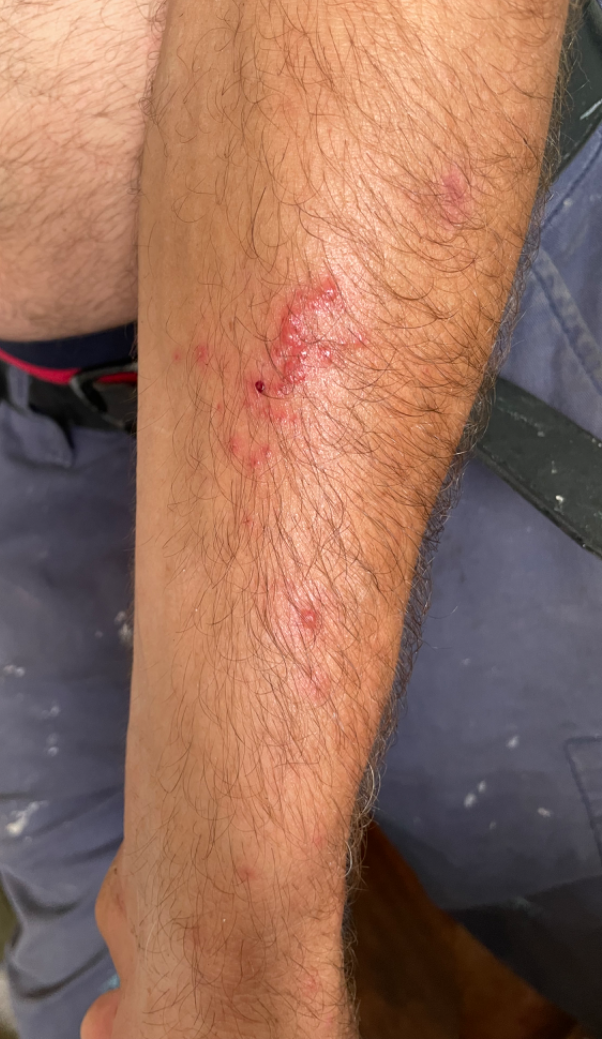  symptoms: itching
  systemic_symptoms: none reported
  shot_type: close-up
  duration: less than one week
  patient_category: a rash
  texture: fluid-filled
  body_site:
    - back of the hand
    - arm
  differential: Allergic Contact Dermatitis